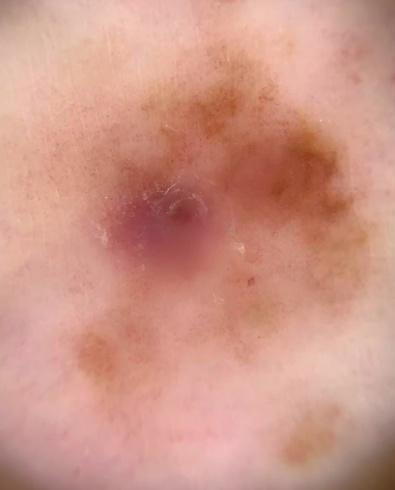{
  "skin_type": "I",
  "image": "contact-polarized dermoscopy",
  "patient": {
    "age_approx": 80,
    "sex": "female"
  },
  "lesion_location": {
    "region": "a lower extremity"
  },
  "diagnosis": {
    "name": "Melanoma",
    "malignancy": "malignant",
    "confirmation": "histopathology"
  }
}